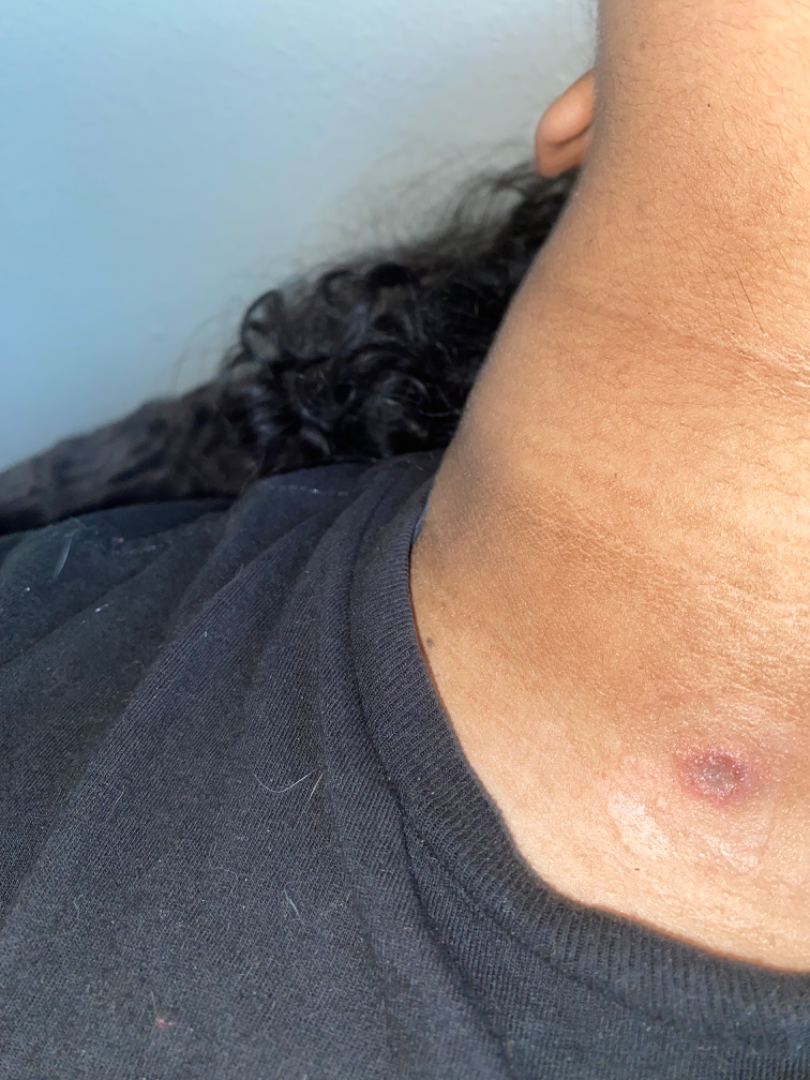Q: How does the patient describe it?
A: a rash
Q: What is the affected area?
A: head or neck and arm
Q: What is the framing?
A: at an angle
Q: Duration?
A: less than one week
Q: What conditions are considered?
A: most consistent with Acne; an alternative is Impetigo